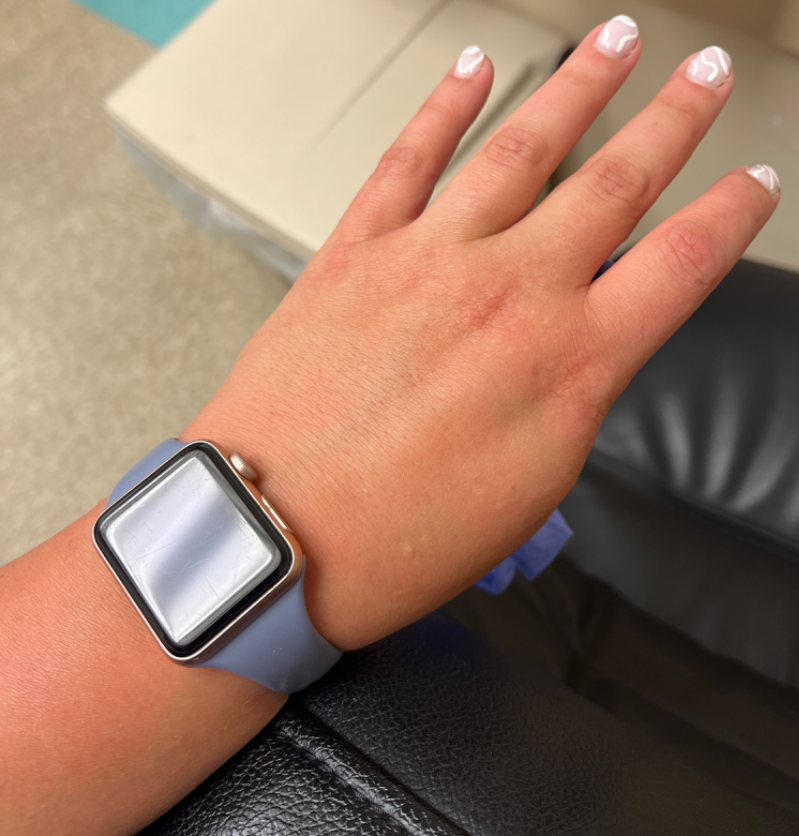Background: An image taken at a distance. The lesion is described as raised or bumpy. Present for less than one week. Fitzpatrick III; human graders estimated Monk skin tone scale 3. Located on the back of the hand and arm. Findings: On teledermatology review: Eczema and Acute and chronic dermatitis were considered with similar weight.